The contributor is a male aged 40–49; close-up view; the leg, front of the torso and arm are involved — 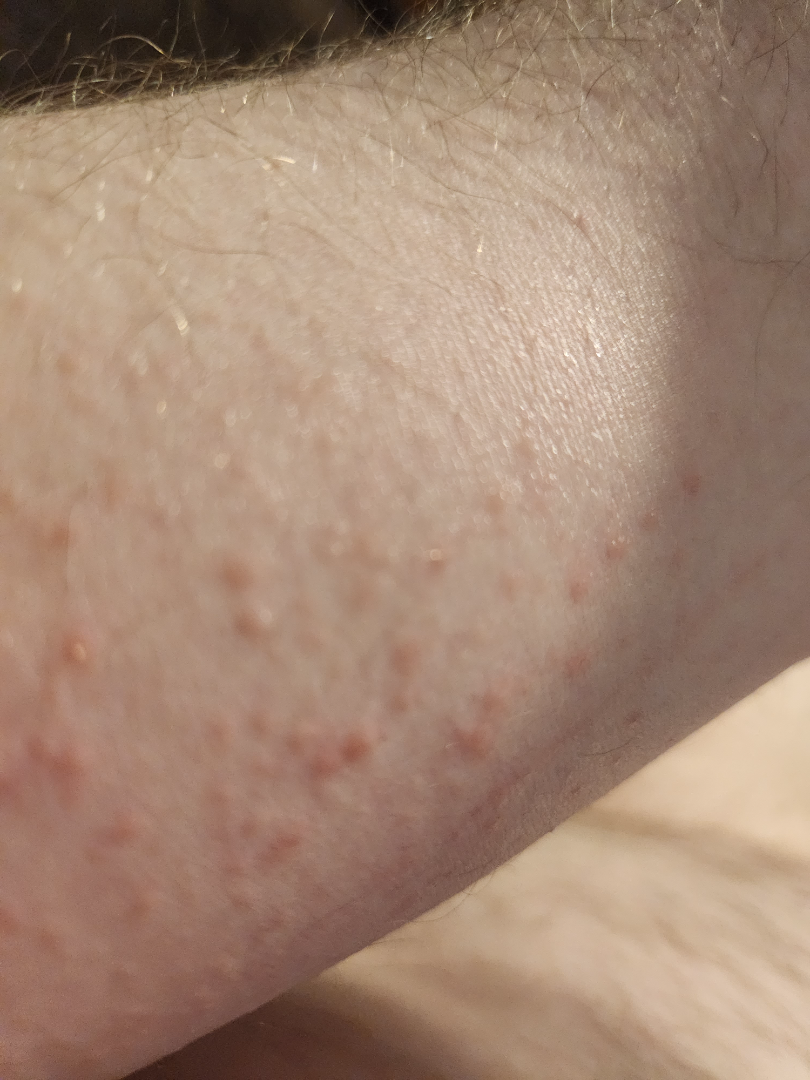Reported lesion symptoms include itching.
The patient considered this a rash.
The condition has been present for less than one week.
The lesion is described as raised or bumpy.
The reviewing dermatologists' impression was: most consistent with Eczema; possibly Irritant Contact Dermatitis; also consider Allergic Contact Dermatitis; a remote consideration is Folliculitis.